Located on the arm, back of the torso, leg and head or neck; an image taken at a distance — 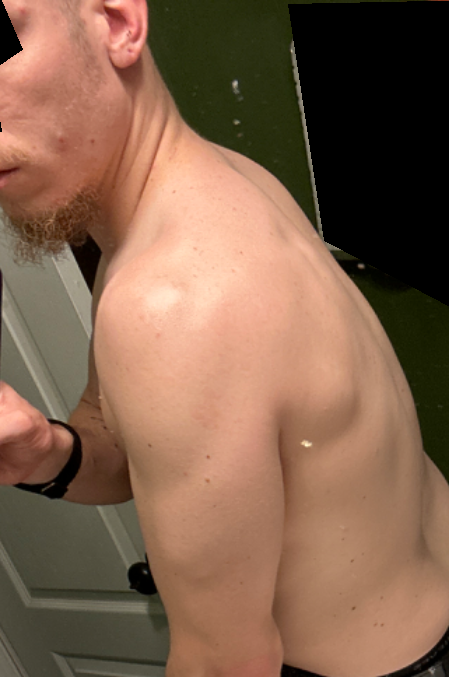Assessment:
The impression on review was Tinea Versicolor.